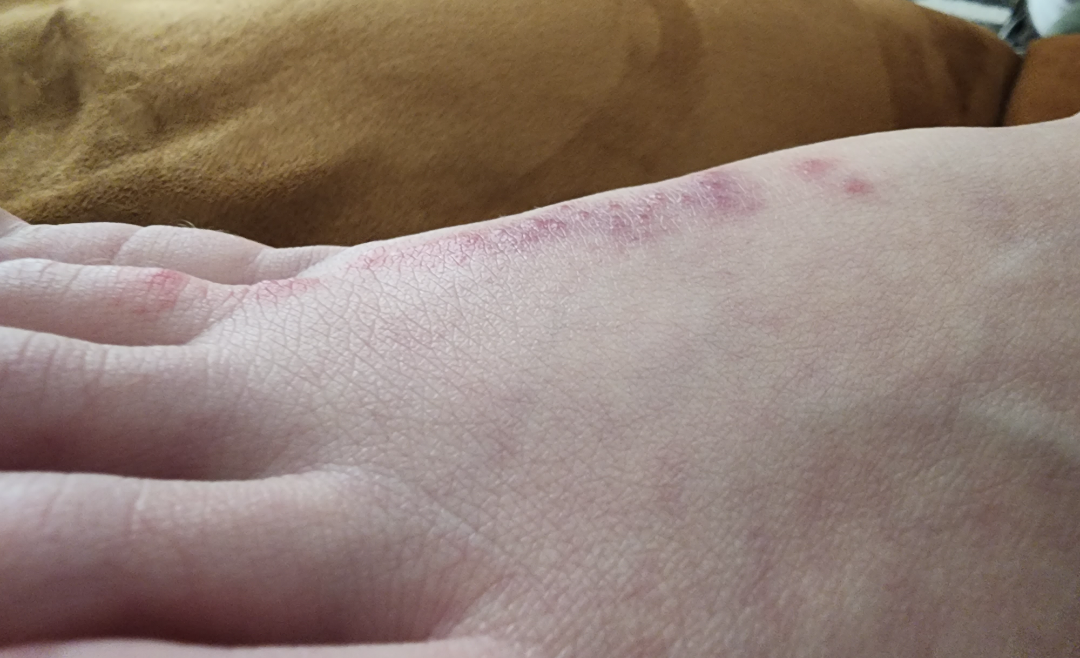History: The photo was captured at an angle. Female patient, age 18–29. The patient notes the condition has been present for less than one week. Reported lesion symptoms include itching, enlargement, bothersome appearance and darkening. Texture is reported as raised or bumpy. The patient considered this a rash. The affected area is the top or side of the foot. No constitutional symptoms were reported. Fitzpatrick phototype II. Impression: Most likely Allergic Contact Dermatitis; also consider Insect Bite; a remote consideration is Herpes Zoster; less probable is Cutaneous larva migrans.